A male patient, aged 68-72 · a dermoscopy image of a single skin lesion.
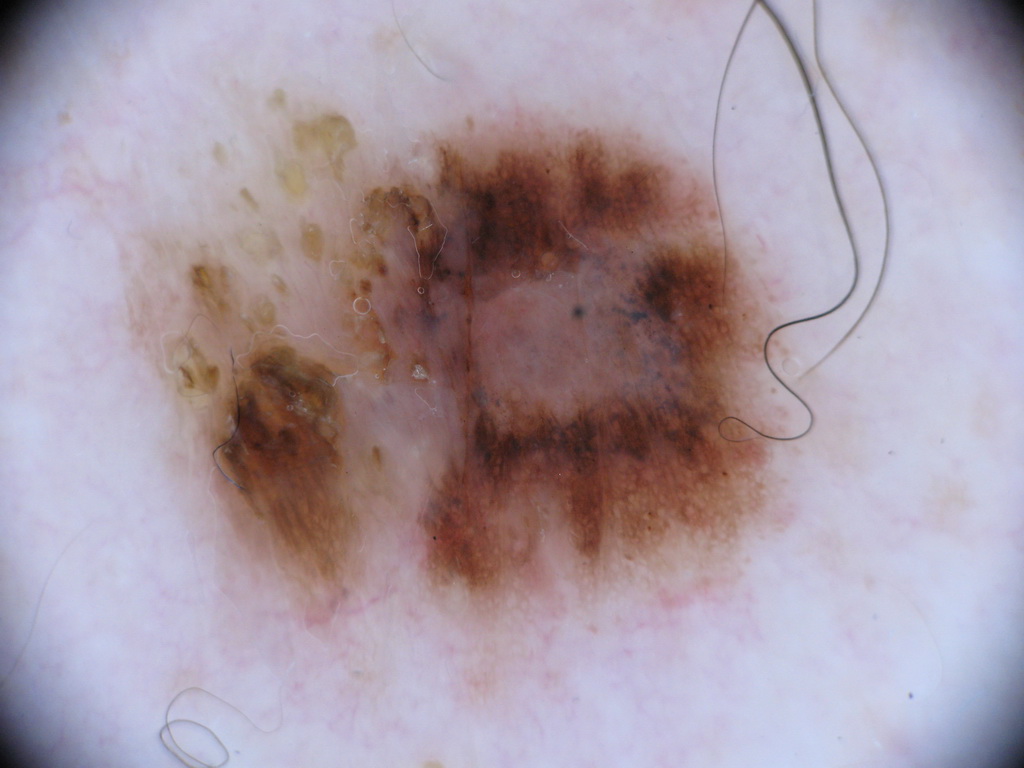  lesion_location:
    bbox_xyxy:
      - 124
      - 88
      - 798
      - 640
  dermoscopic_features:
    present:
      - pigment network
    absent:
      - streaks
      - milia-like cysts
      - negative network
      - globules
  diagnosis:
    name: melanocytic nevus
    malignancy: benign
    lineage: melanocytic
    provenance: clinical